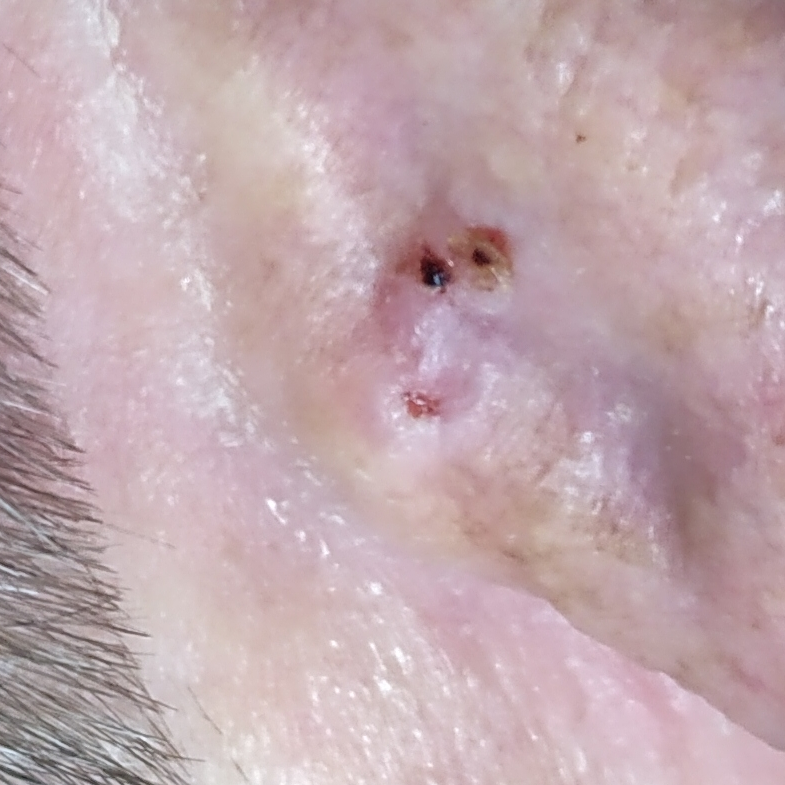Histopathologically confirmed as a basal cell carcinoma.